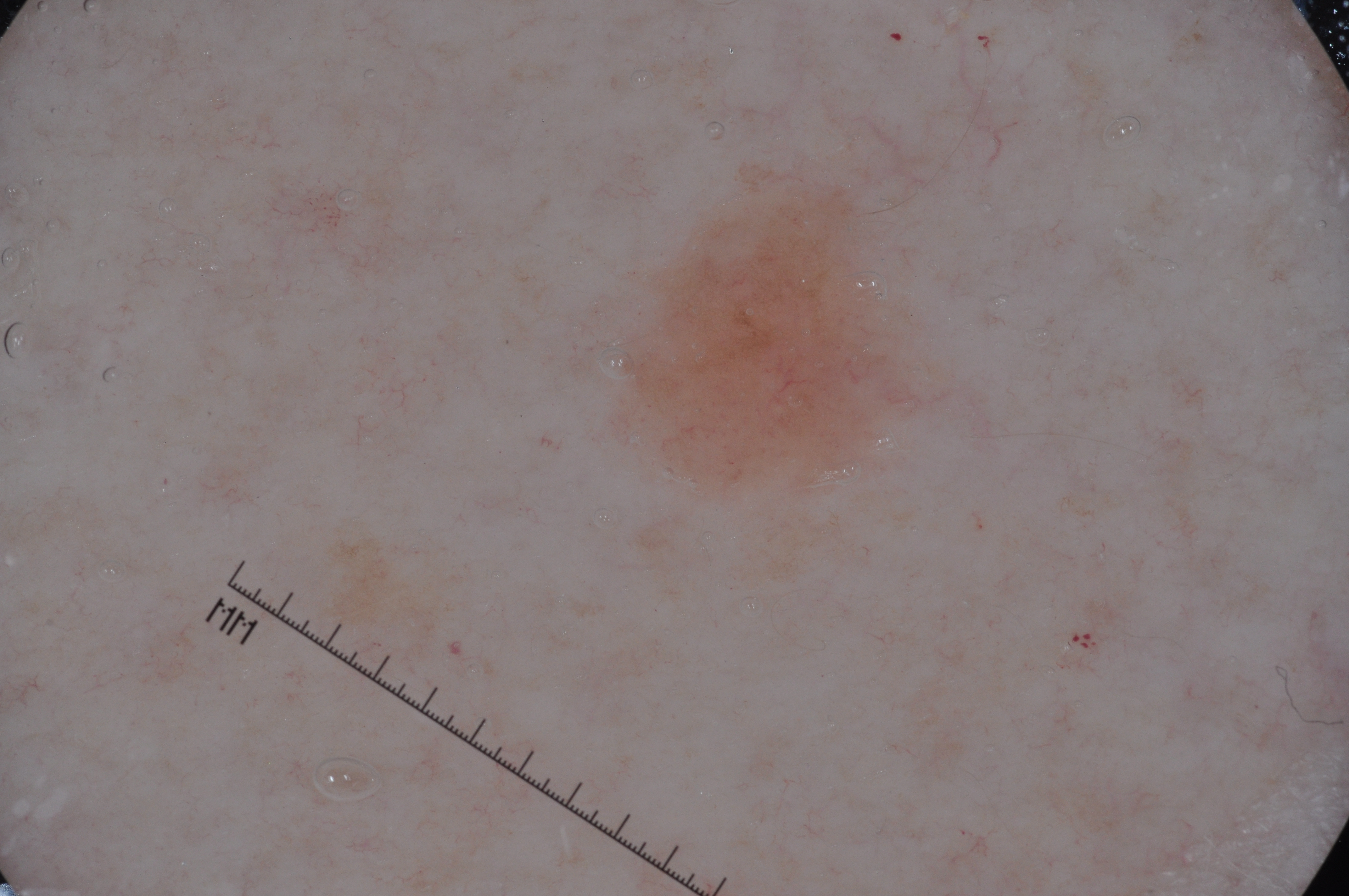A skin lesion imaged with a dermatoscope. Dermoscopic examination shows pigment network; no milia-like cysts, streaks, or negative network. In (x1, y1, x2, y2) order, the lesion spans box(633, 182, 916, 483). The lesion takes up about 5% of the image. Consistent with a melanocytic nevus, a benign skin lesion.